A dermoscopic photograph of a skin lesion:
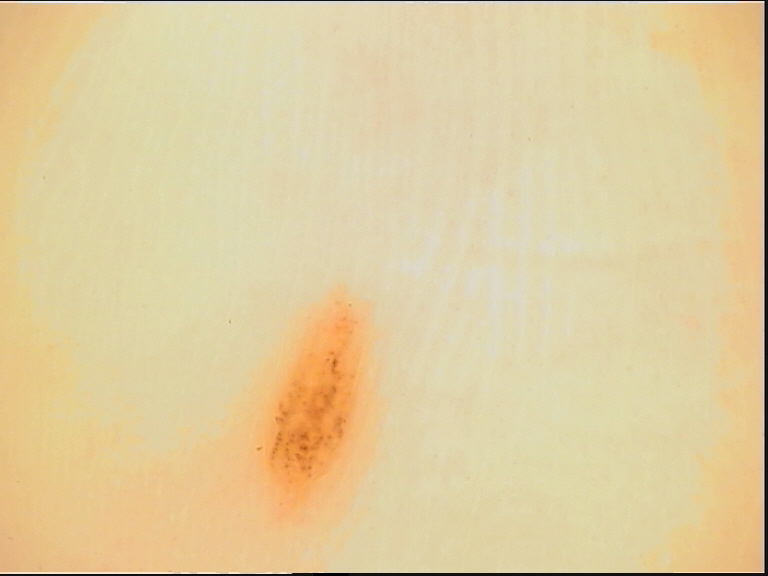- diagnosis — acral dysplastic junctional nevus (expert consensus)